A dermoscopy image of a single skin lesion · the patient was assessed as FST II · a male patient about 65 years old:
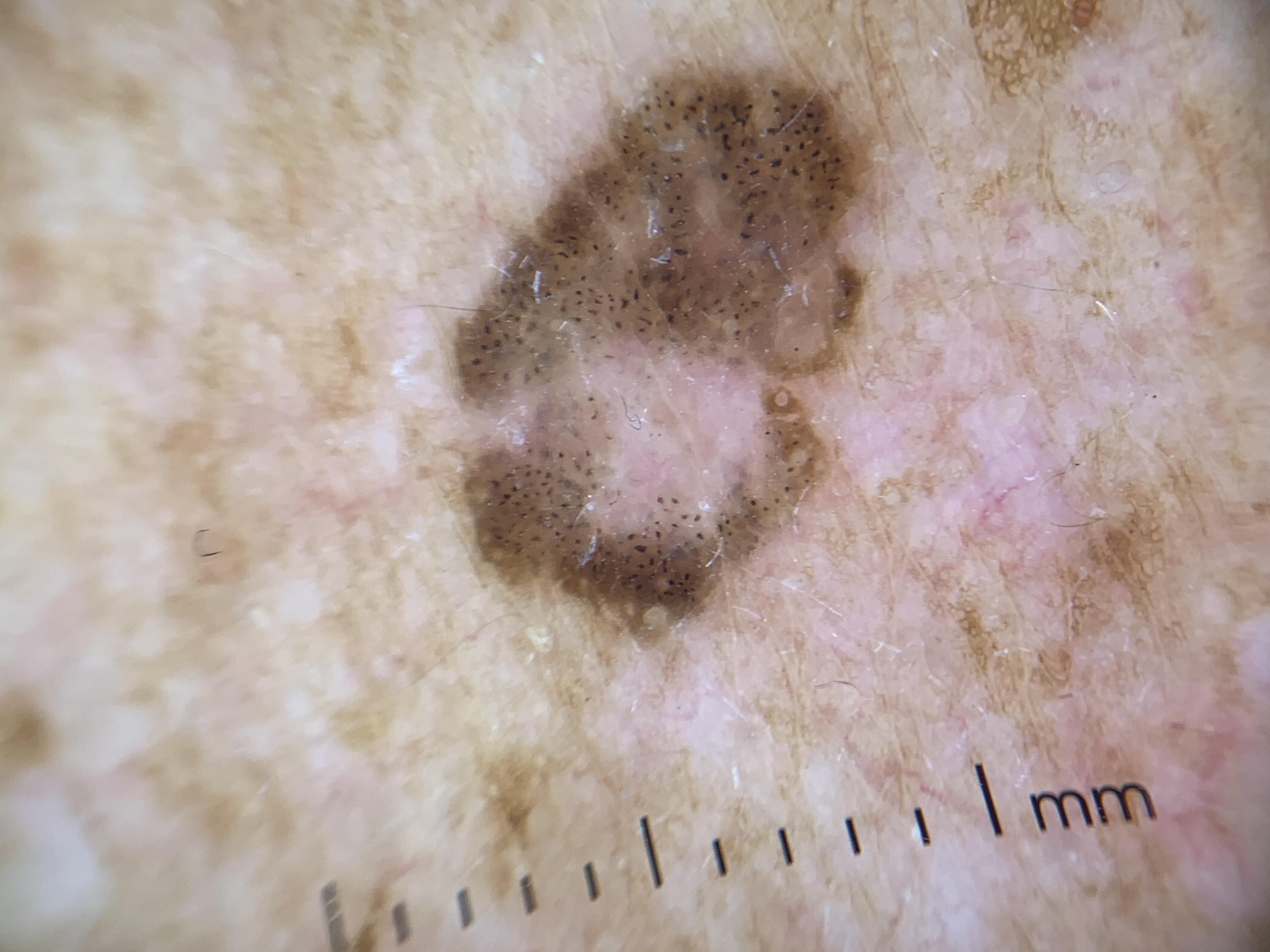{
  "lesion_location": {
    "region": "the trunk",
    "detail": "the posterior trunk"
  },
  "diagnosis": {
    "name": "Seborrheic keratosis",
    "malignancy": "benign",
    "confirmation": "histopathology",
    "lineage": "epidermal"
  }
}